Female patient, age 60–69; located on the back of the torso; the photograph was taken at an angle: 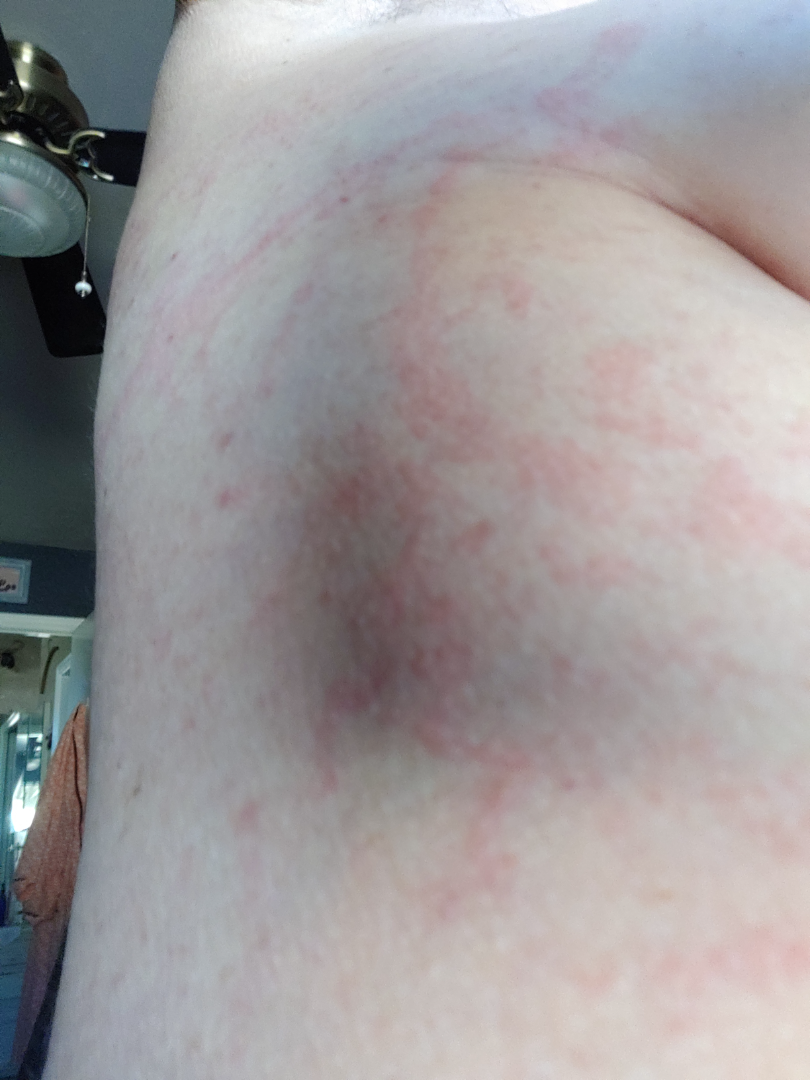The reviewing dermatologists' impression was: most consistent with Urticaria; lower on the differential is Pruritic urticarial papules and plaques of pregnancy; less probable is Eczema; less likely is Allergic Contact Dermatitis.